Located on the leg. This is a close-up image:
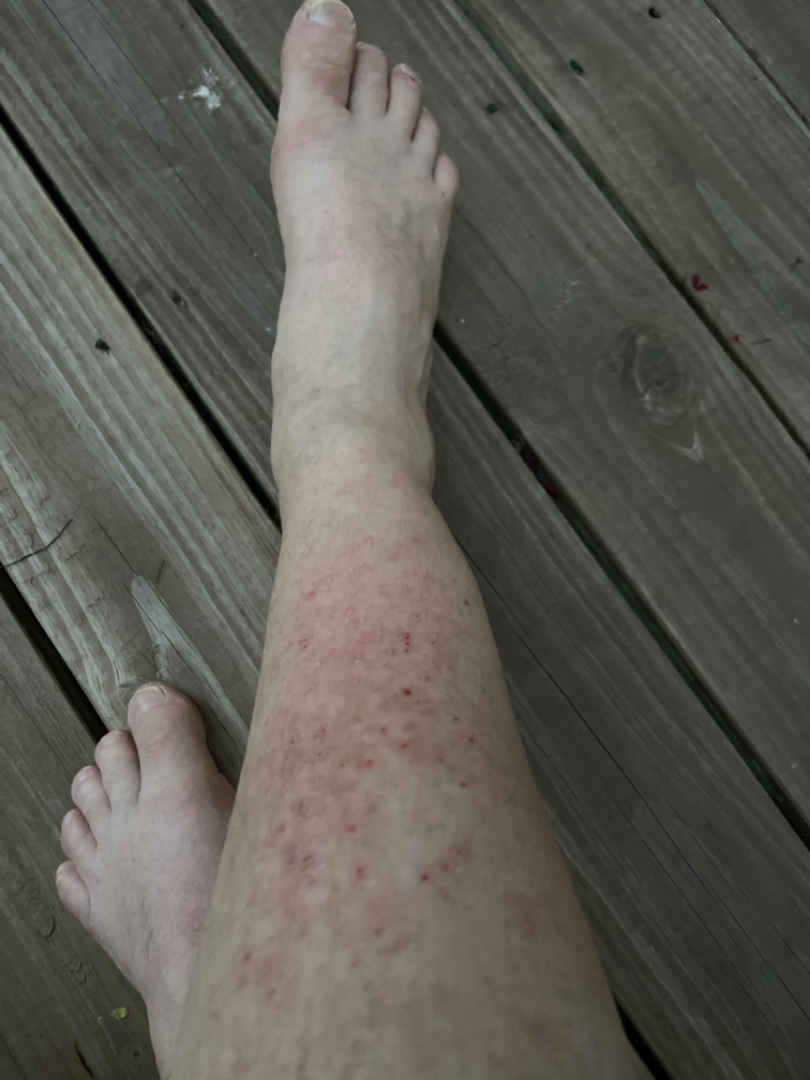differential: Eczema, Stasis Dermatitis and Allergic Contact Dermatitis were each considered, in no particular order